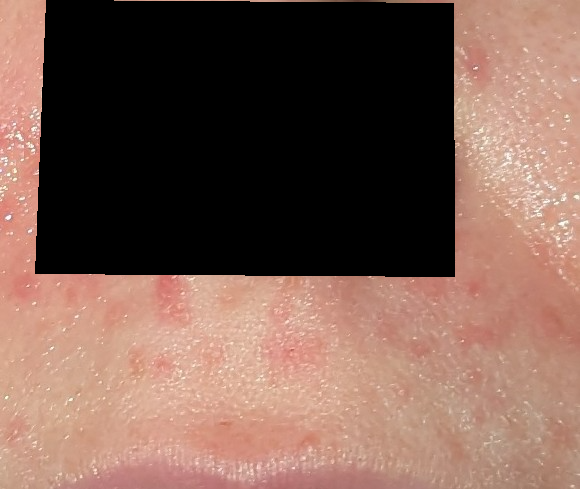assessment — indeterminate; texture — raised or bumpy and rough or flaky; associated systemic symptoms — fatigue; present for — one to three months; photo taken — close-up; subject — female, age 30–39; self-categorized as — a rash; site — head or neck.